A dermoscopic photograph of a skin lesion: 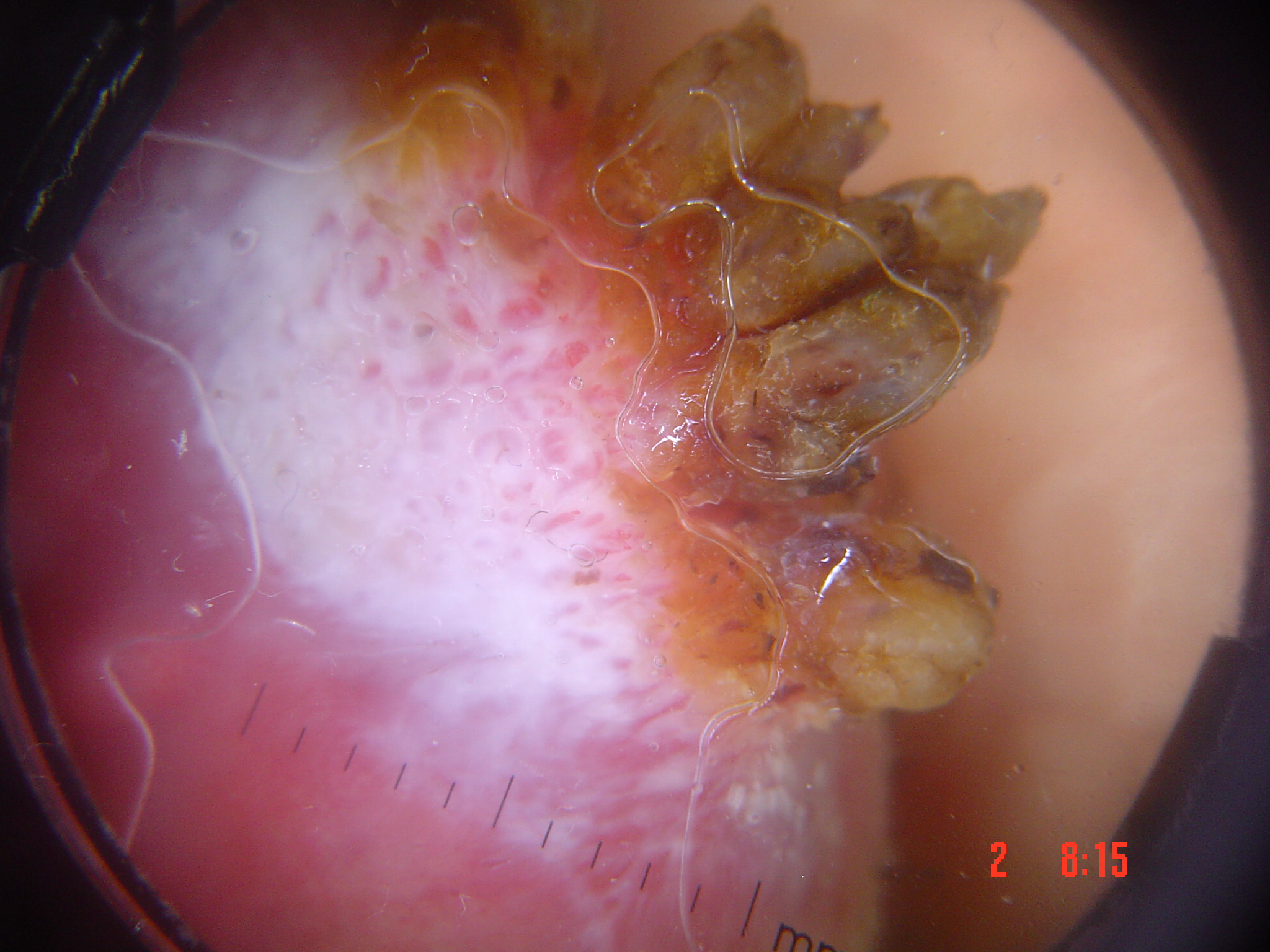pathology=squamous cell carcinoma (biopsy-proven).